The photograph is a close-up of the affected area:
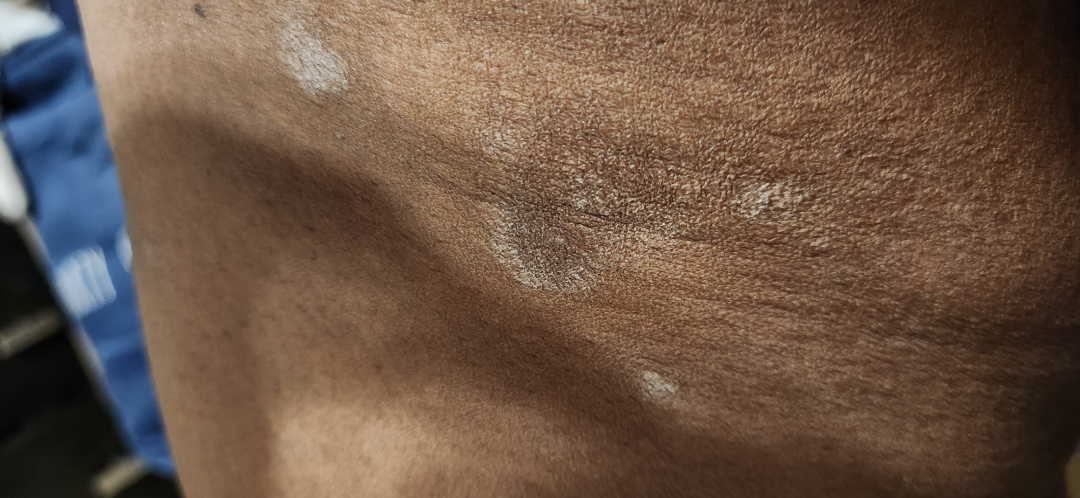assessment = not assessable | patient-reported symptoms = none reported | duration = three to twelve months | self-categorized as = skin that appeared healthy to them | skin tone = Fitzpatrick phototype V; non-clinician graders estimated Monk Skin Tone 7 (US pool) or 5 (India pool) | other reported symptoms = none reported.